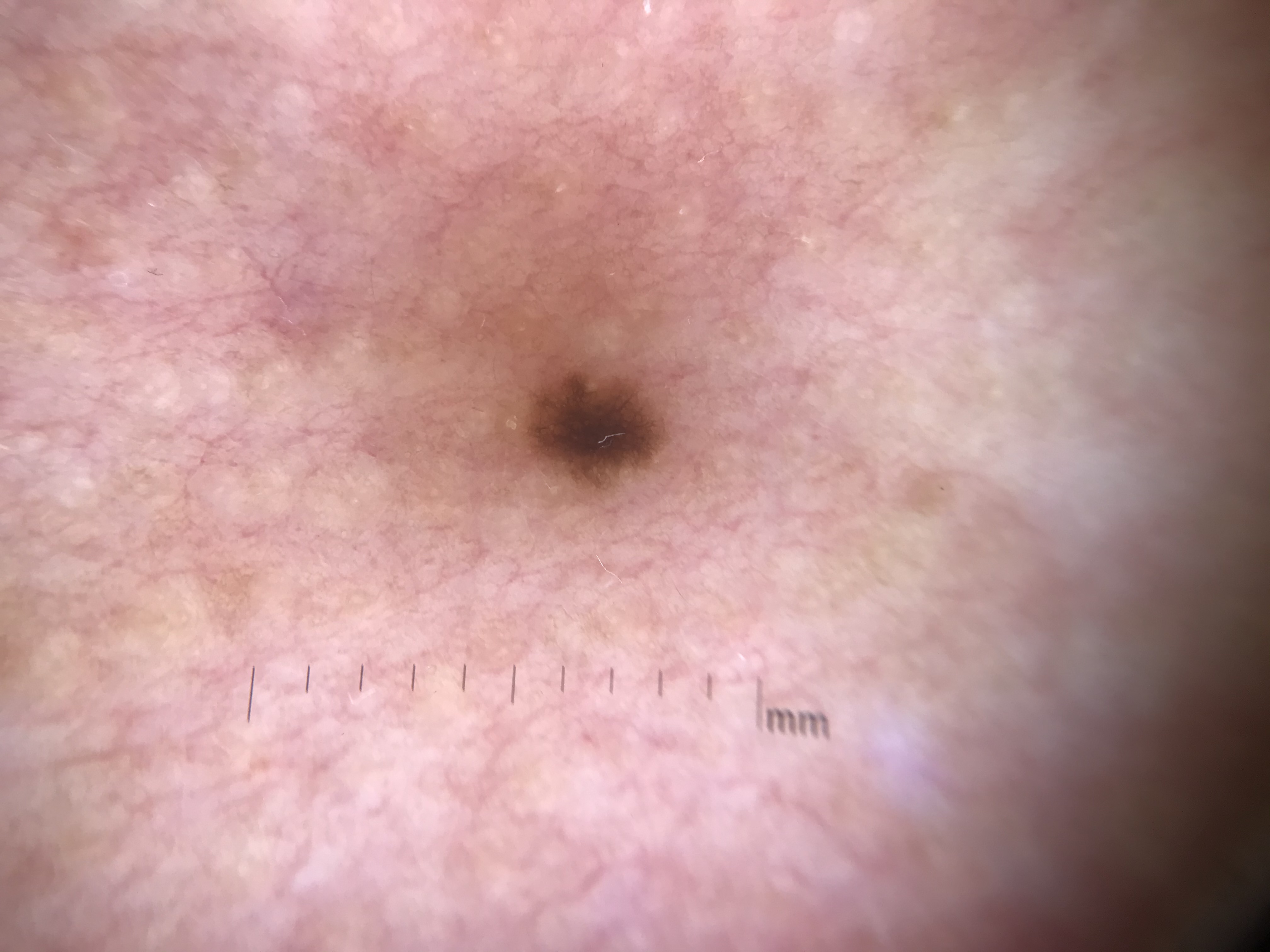A dermoscopic photograph of a skin lesion.
The morphology is that of a banal lesion.
Classified as a junctional nevus.